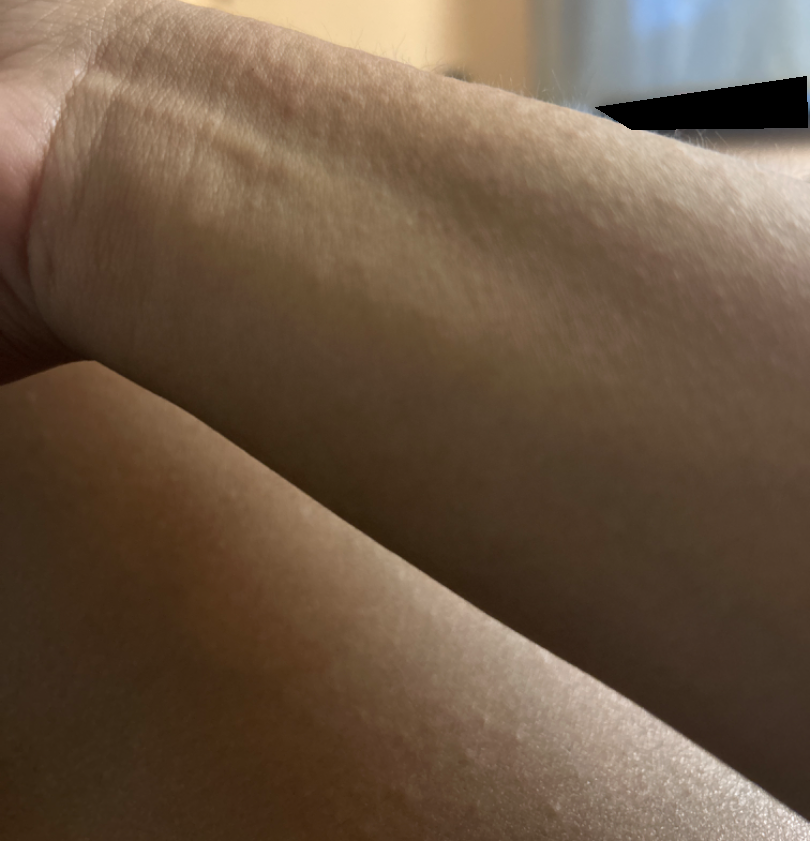Assessment:
On photographic review: Allergic Contact Dermatitis (primary); Acute dermatitis, NOS (possible); Miliaria (remote); Hypersensitivity (remote); Eczema (remote).